A male subject aged 73 to 77. The chart documents a prior melanoma. Dermoscopy of a skin lesion.
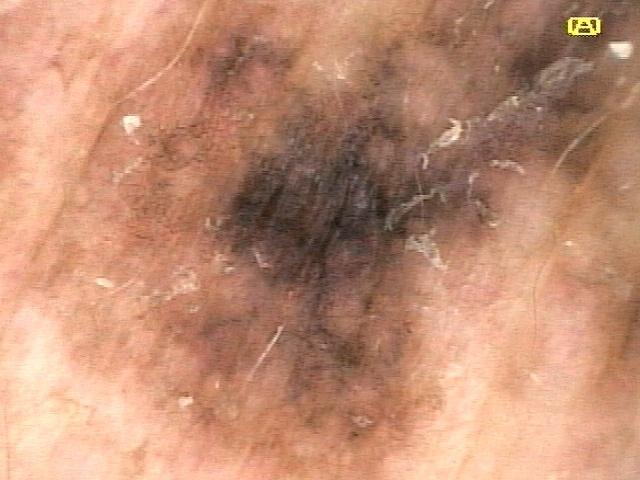The lesion is on the trunk, specifically the posterior trunk. Histopathologically confirmed as a melanoma.